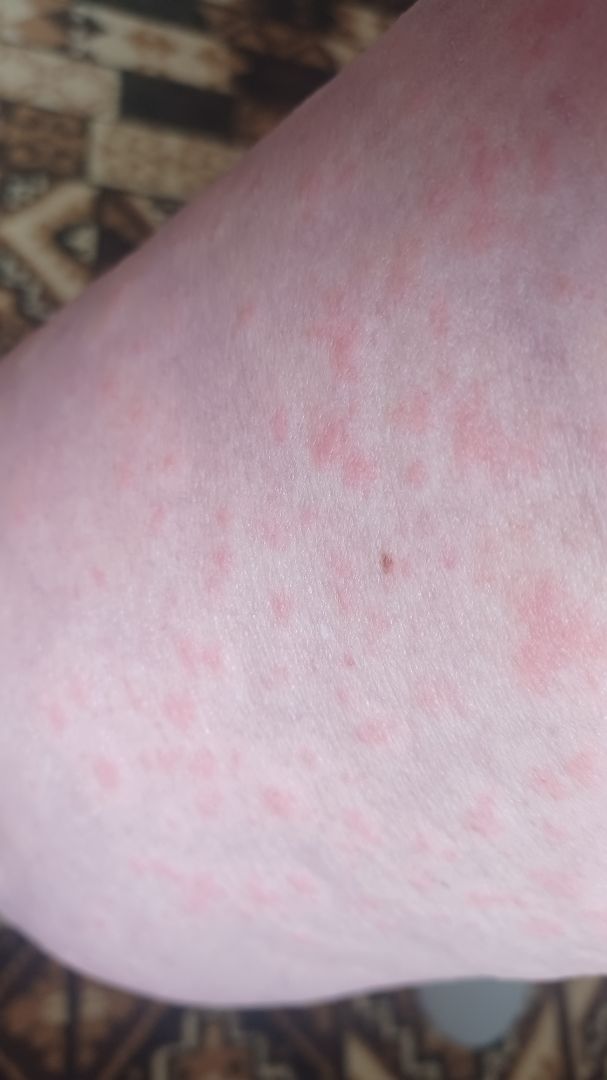The case was difficult to assess from the available photograph. The leg, arm and front of the torso are involved. Female subject, age 60–69. An image taken at an angle.